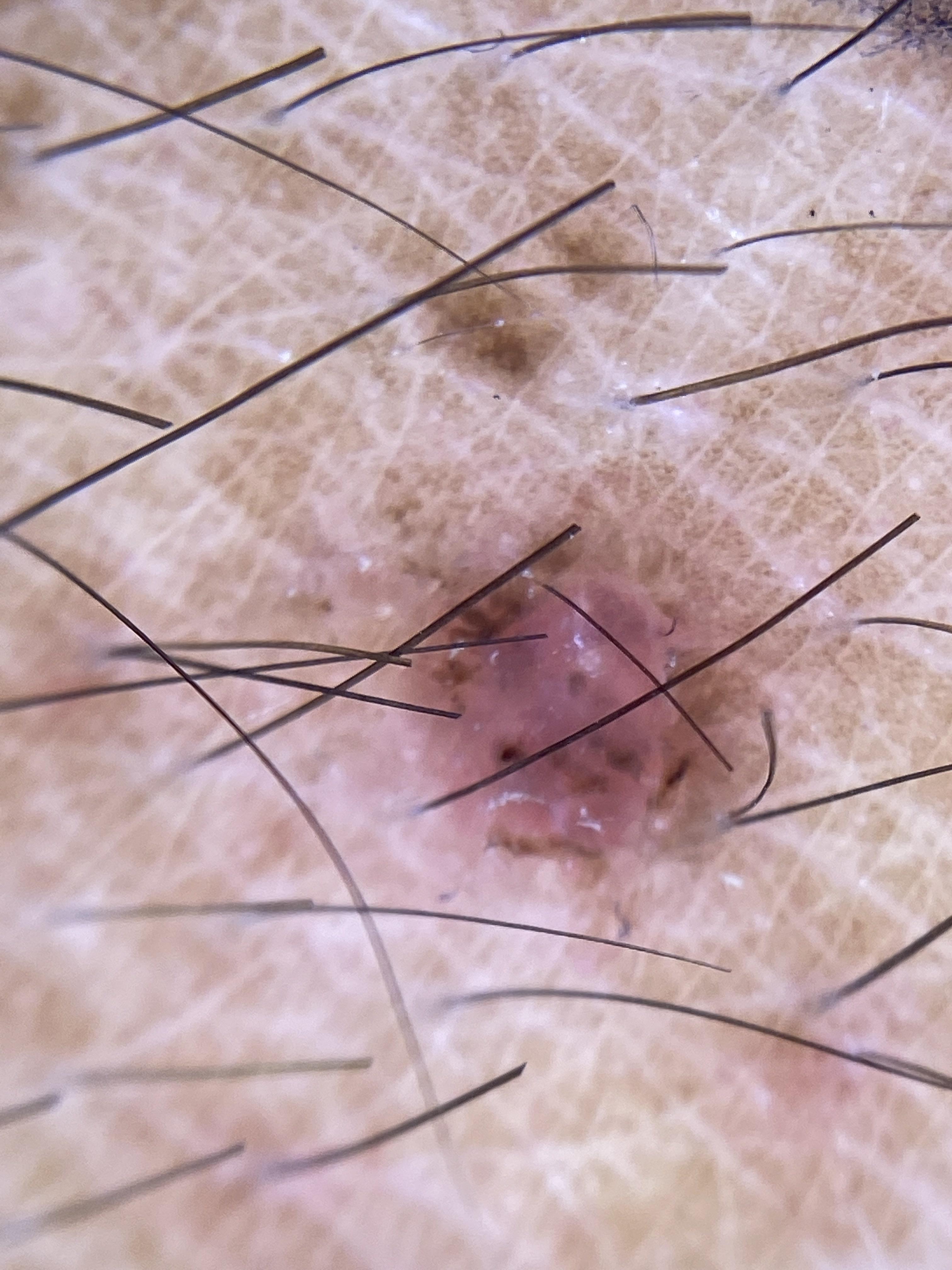pathology = Basal cell carcinoma (biopsy-proven).